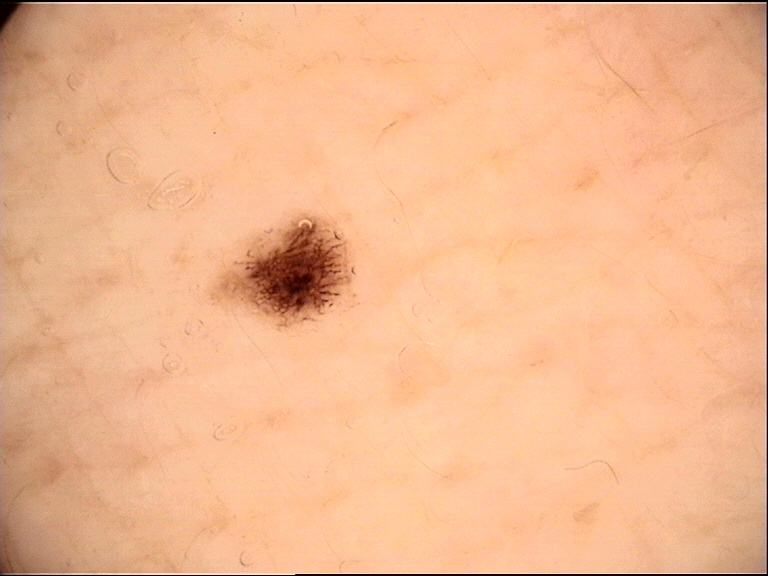modality=dermoscopy | assessment=acral dysplastic junctional nevus (expert consensus).